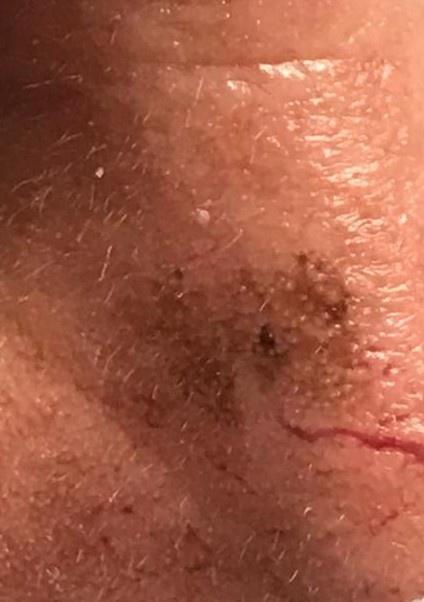Image and clinical context: A clinical photograph showing a skin lesion in context. A male patient in their mid-70s. The lesion is located on the head or neck. Pathology: The biopsy diagnosis was a squamous cell carcinoma.